A dermoscopic image of a skin lesion.
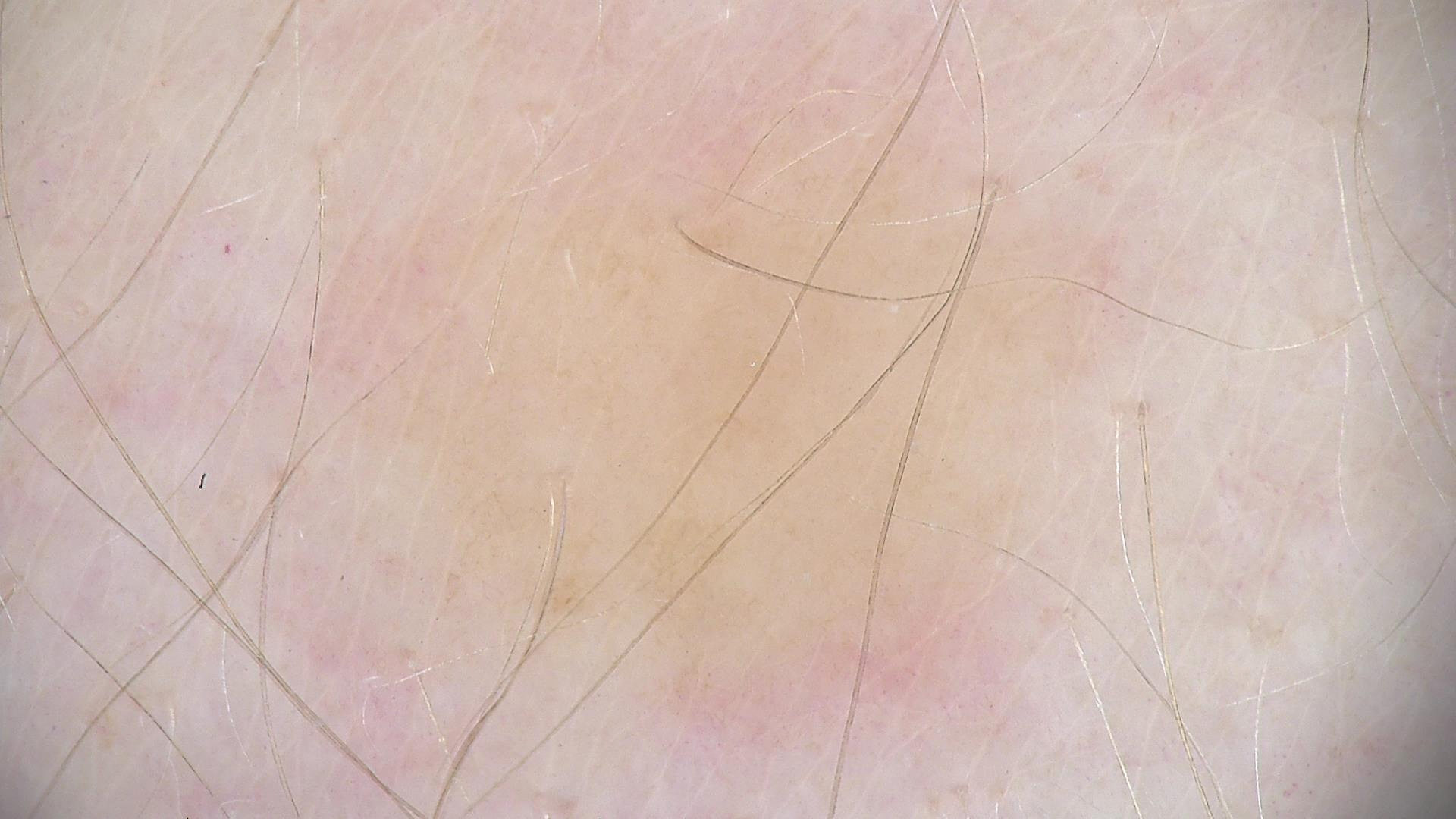The architecture is that of a fibro-histiocytic lesion. Labeled as a dermatofibroma.